A dermoscopic close-up of a skin lesion.
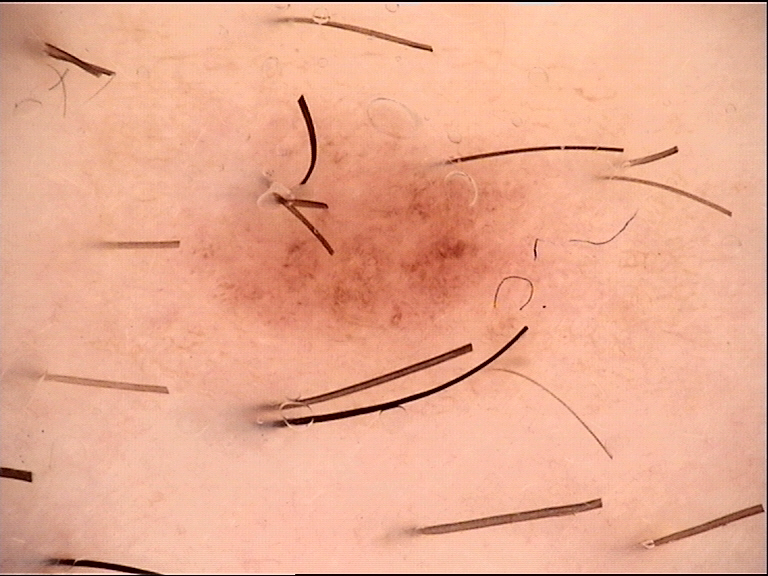Impression:
The diagnosis was a benign lesion — a dysplastic junctional nevus.